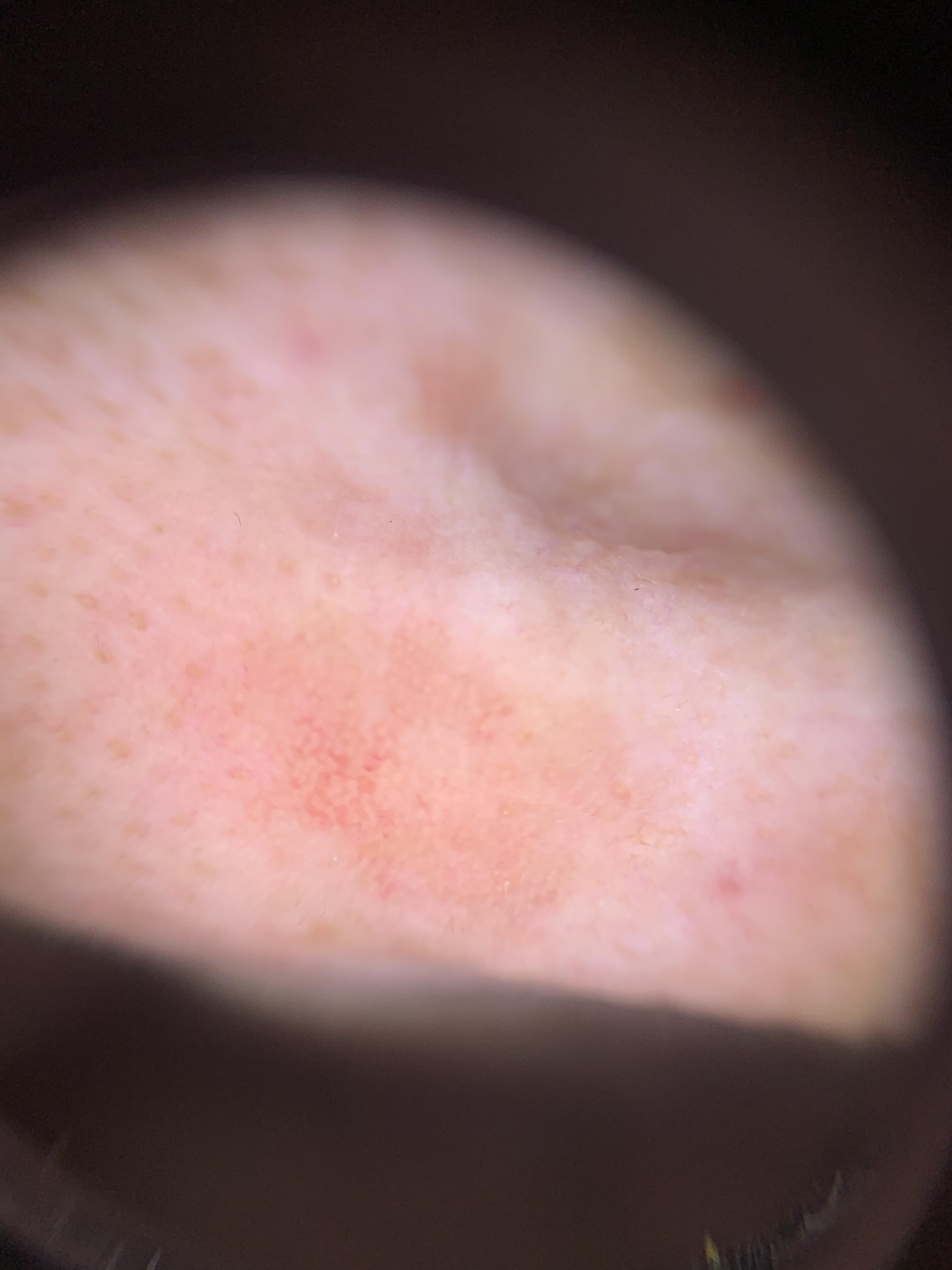The patient is Fitzpatrick phototype II. A female subject aged 68-72. The lesion was found on the head or neck. The clinical impression was a lesion of epidermal origin — a solar or actinic keratosis.